The lesion involves the head or neck, front of the torso, arm and leg · close-up view · the contributor is female — 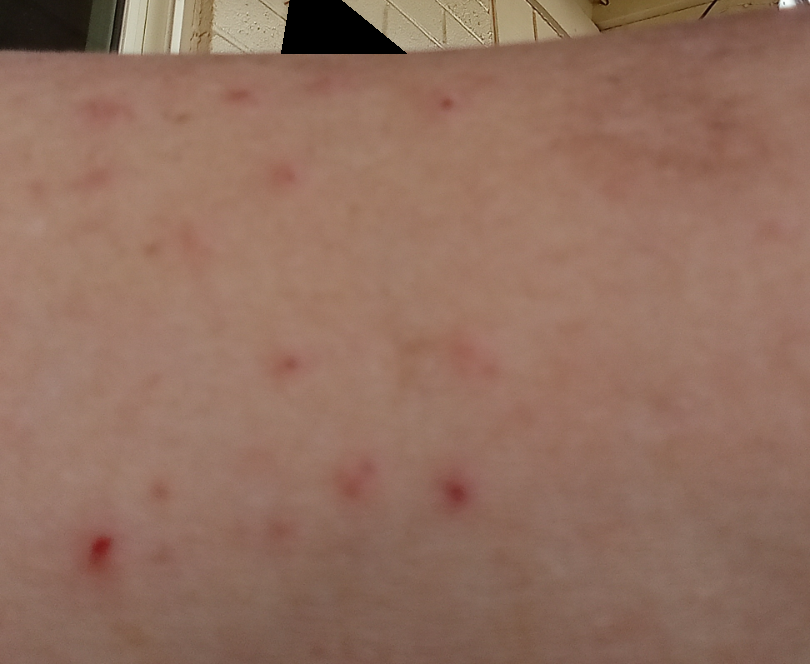Case summary:
* assessment — indeterminate from the photograph